The contributor is 40–49, male. The arm is involved. The photograph is a close-up of the affected area:
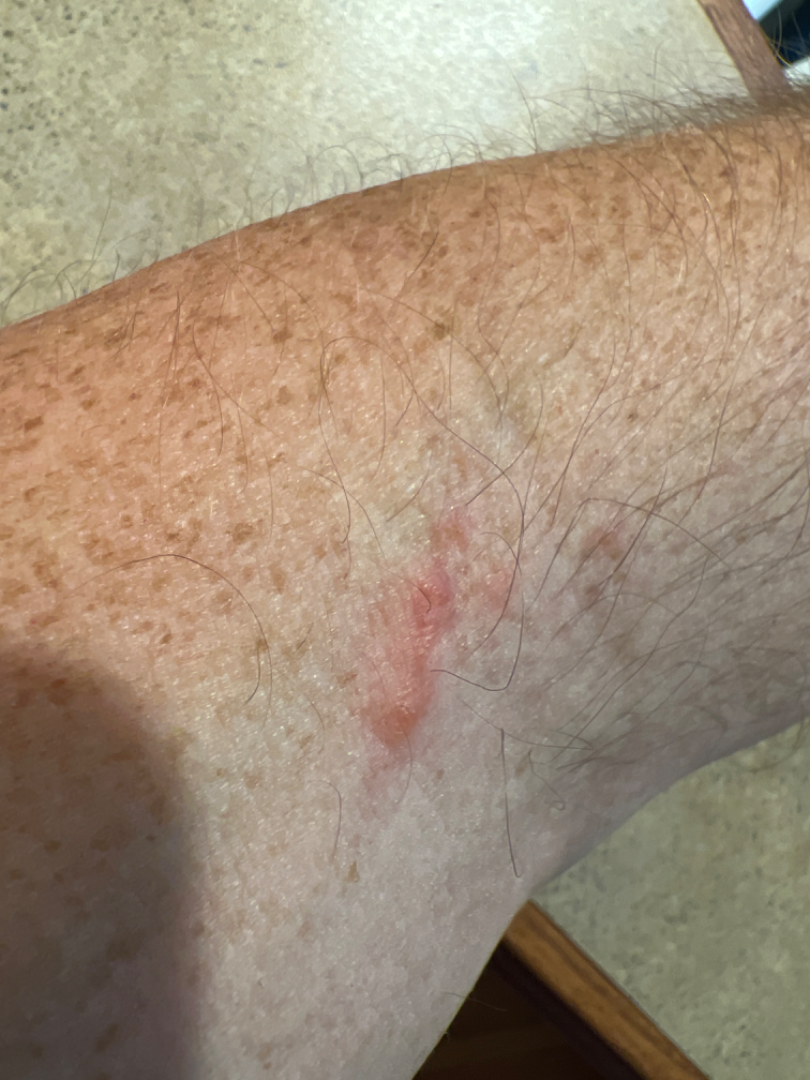Review:
On independent review by the dermatologists: Contact dermatitis (favored); Insect Bite (possible); Allergic Contact Dermatitis (possible); Urticaria (lower probability).